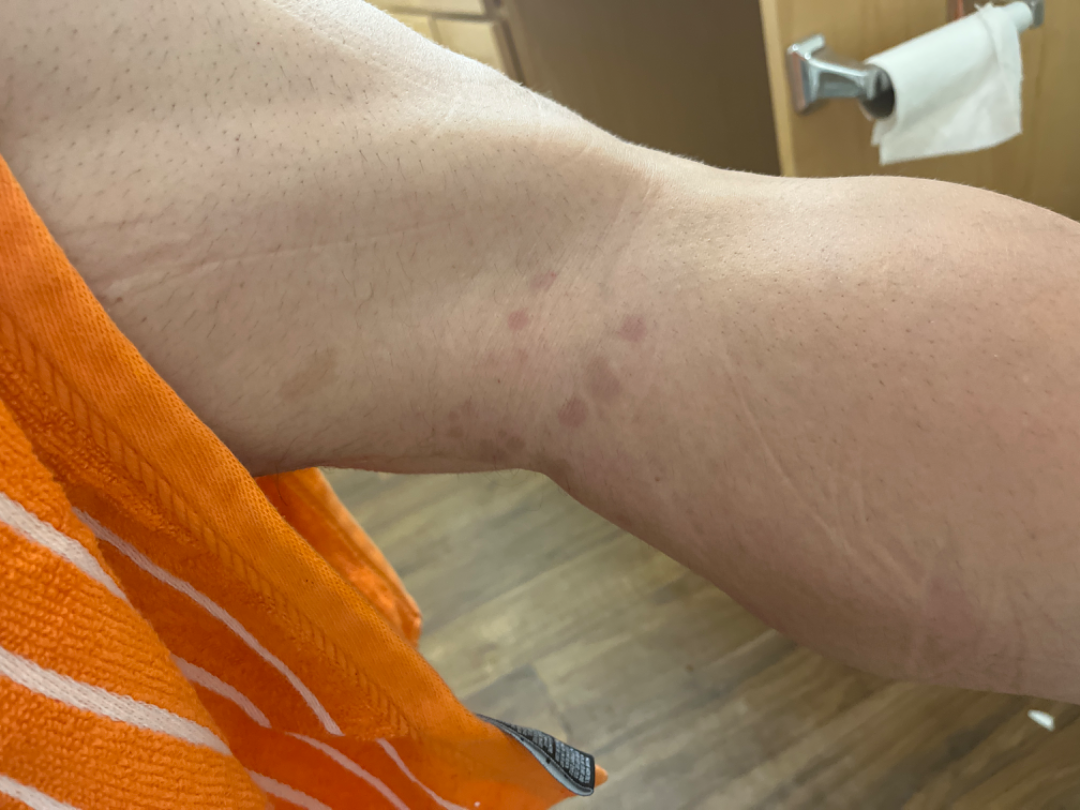Notes:
• assessment — could not be assessed